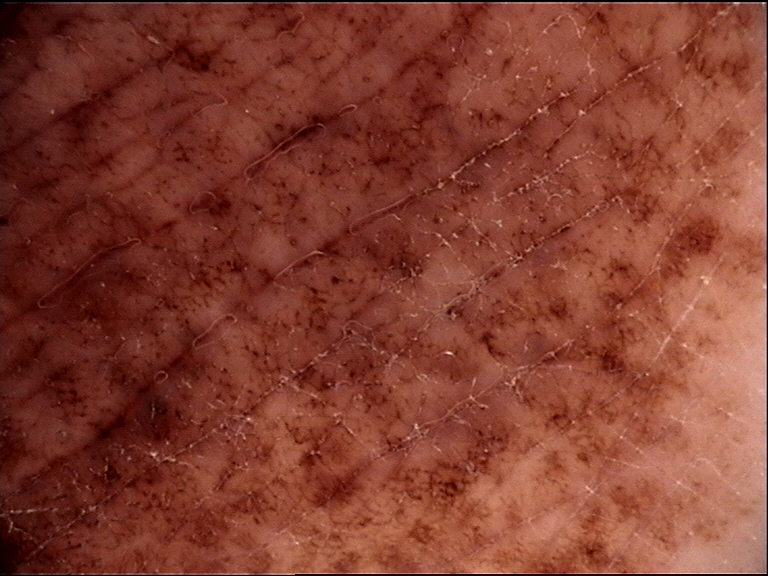Q: What kind of image is this?
A: dermatoscopy
Q: How is the lesion classified?
A: banal
Q: What is the diagnosis?
A: congenital compound nevus (expert consensus)